A dermoscopic photograph of a skin lesion.
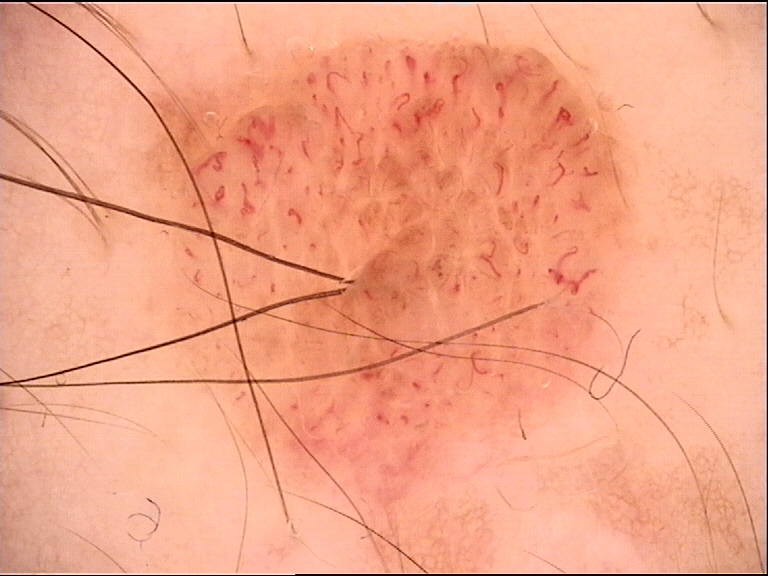classification = banal
assessment = dermal nevus (expert consensus)